A female subject in their mid-60s; a clinical photograph showing a skin lesion; FST II:
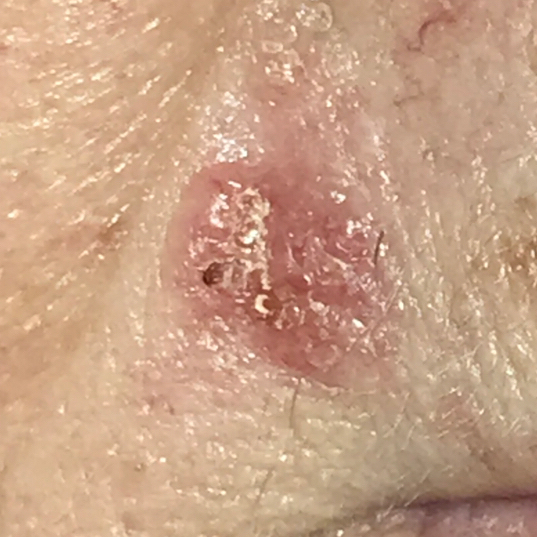Clinical context:
The lesion involves the face. The lesion measures approximately 8 × 7 mm. The patient describes that the lesion itches and is elevated, but has not bled and does not hurt.
Diagnosis:
Histopathology confirmed a basal cell carcinoma.